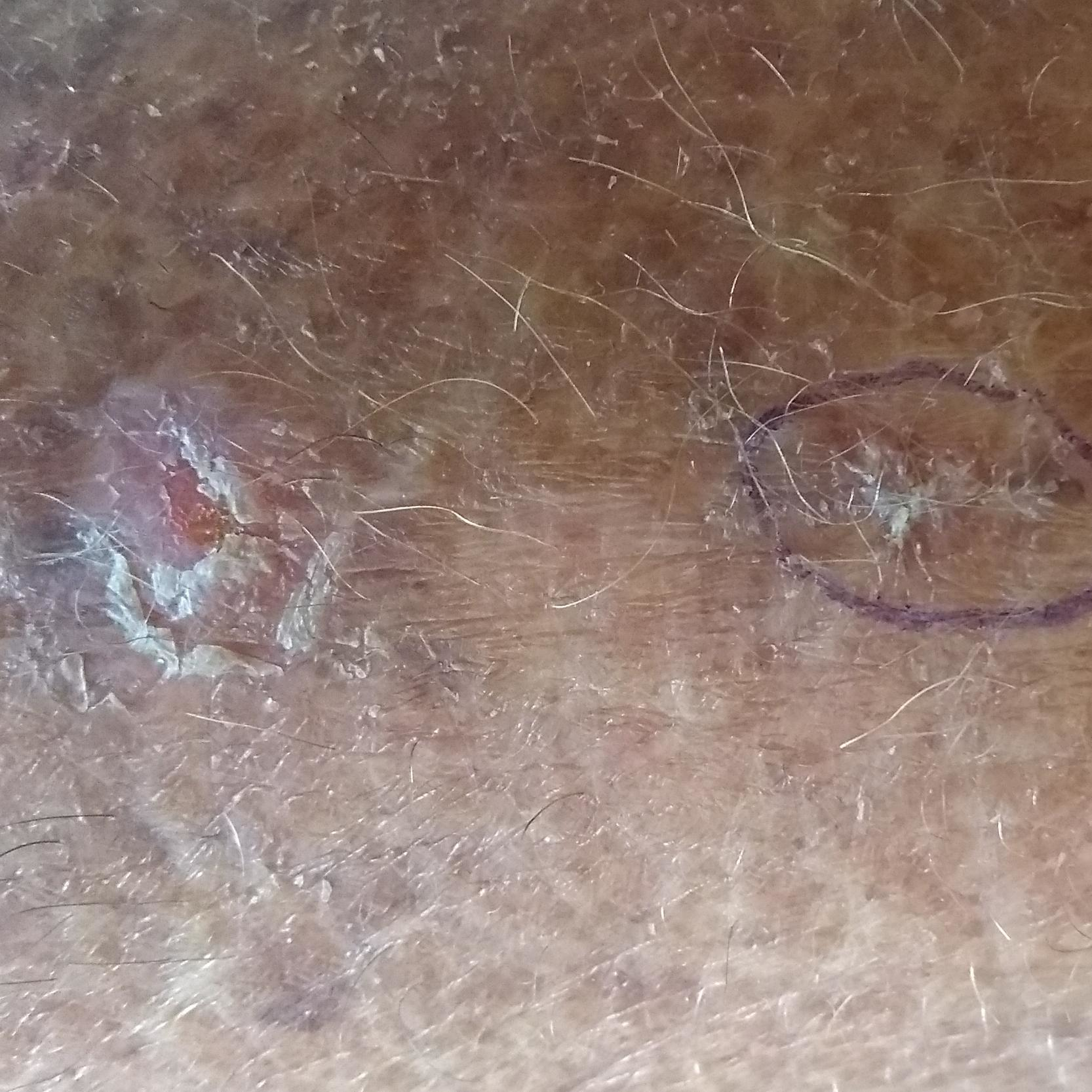skin type — III; exposures — prior malignancy (patient or family), pesticide exposure, prior skin cancer (patient or family); imaging — clinical photo; patient-reported symptoms — elevation, itching, growth; impression — actinic keratosis (clinical consensus).